The patient is 18–29, male; close-up view; the lesion involves the leg: 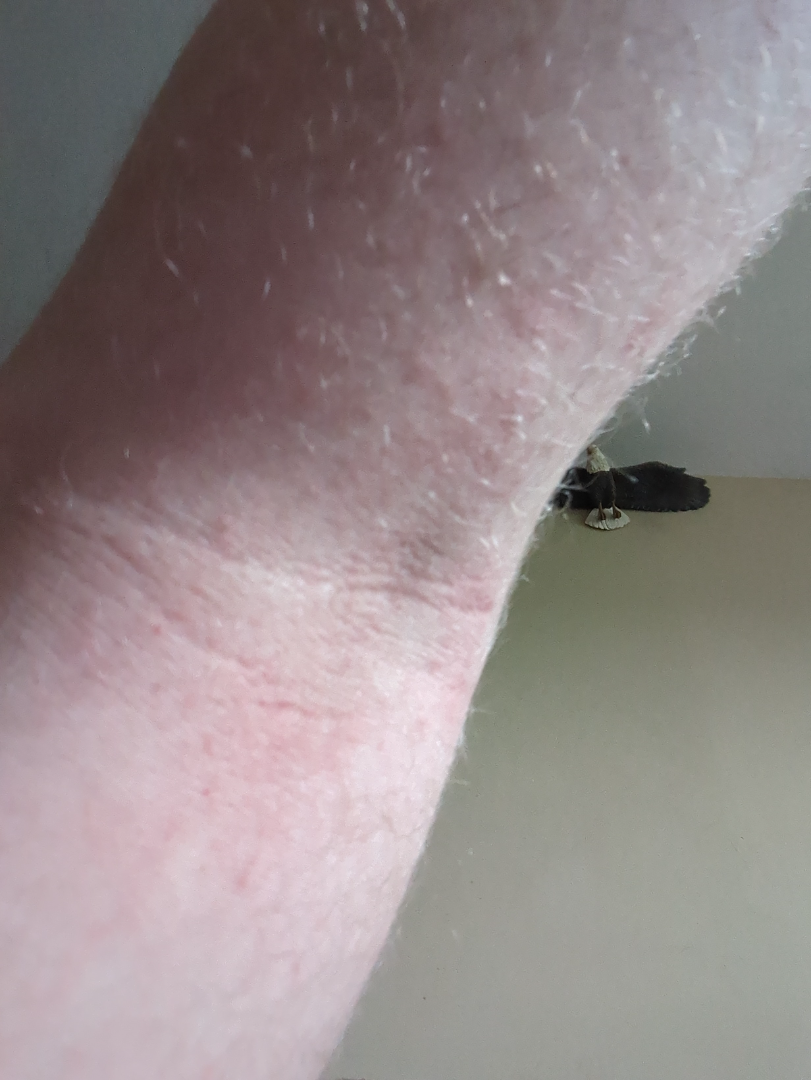{
  "systemic_symptoms": "none reported",
  "duration": "one to three months",
  "patient_category": "a rash",
  "texture": "raised or bumpy",
  "symptoms": [
    "bleeding",
    "itching"
  ],
  "differential": {
    "leading": [
      "Eczema"
    ]
  }
}